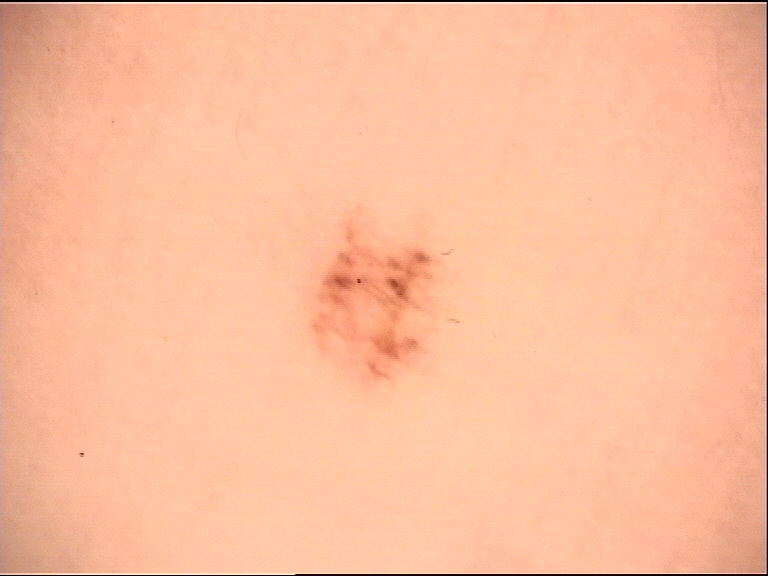A dermoscopic close-up of a skin lesion. Labeled as an acral dysplastic junctional nevus.